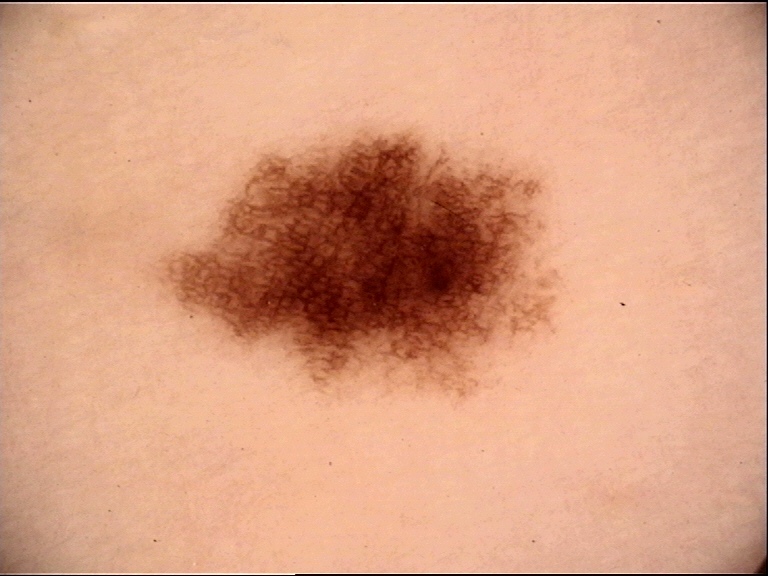Findings: A dermoscopic close-up of a skin lesion. Conclusion: Classified as a banal lesion — a junctional nevus.